The arm is involved · this image was taken at an angle · the patient reports the lesion is flat · the condition has been present for about one day · the patient also reports joint pain · the patient described the issue as skin that appeared healthy to them: 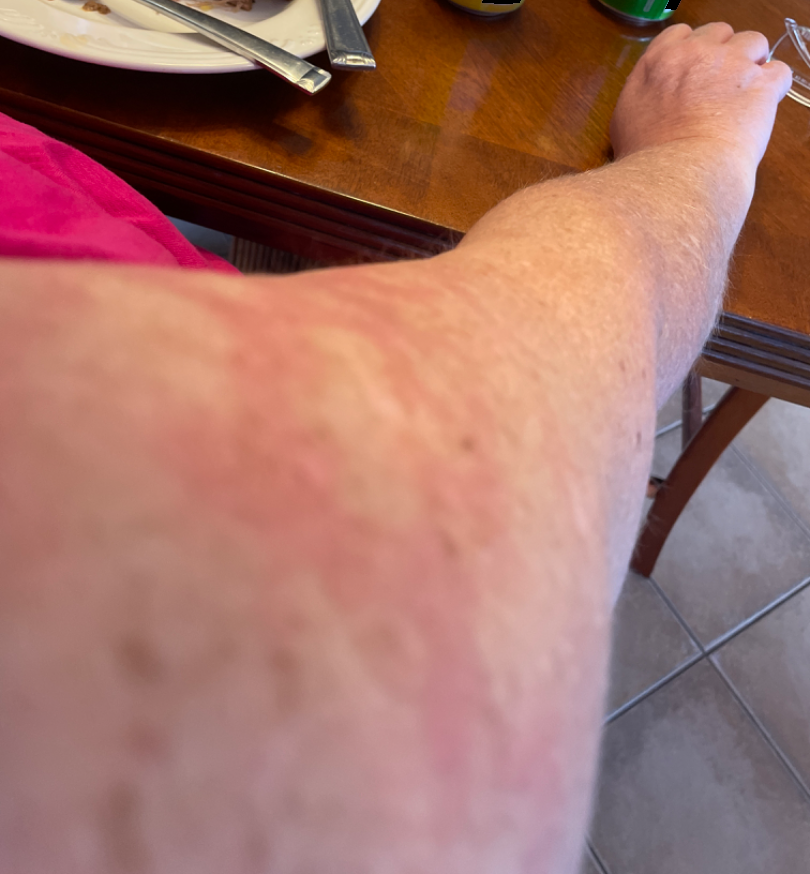On dermatologist assessment of the image, Livedo reticularis, Erythema ab igne and Livedoid vasculopathy were each considered, in no particular order.